A male subject 57 years old · by history, prior skin cancer (patient or family) · a clinical photograph showing a skin lesion · recorded as skin type IV: 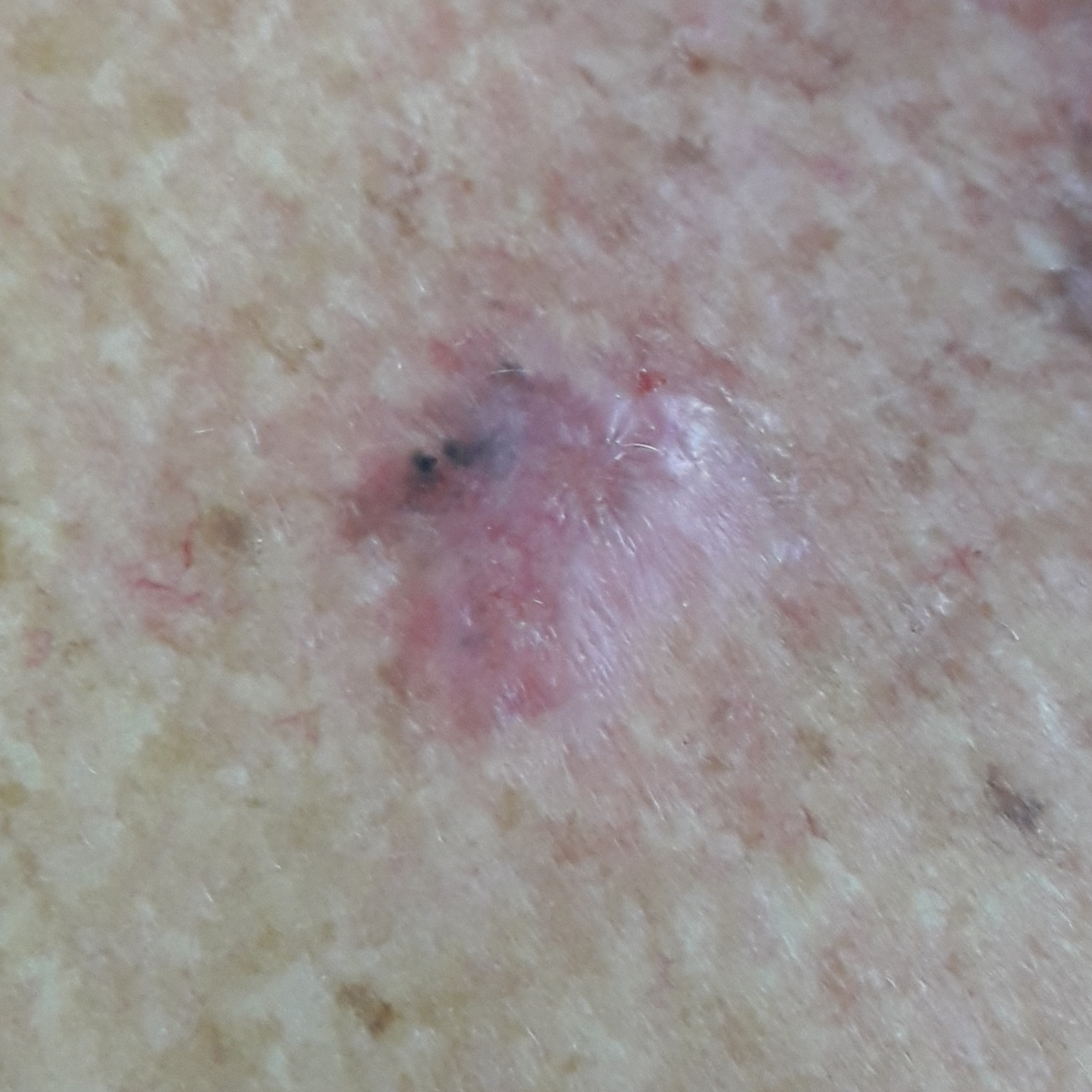The lesion was found on the chest. The lesion measures approximately 12 × 10 mm. The patient describes that the lesion has grown, is elevated, itches, and hurts. Histopathology confirmed a basal cell carcinoma.